A dermatoscopic image of a skin lesion.
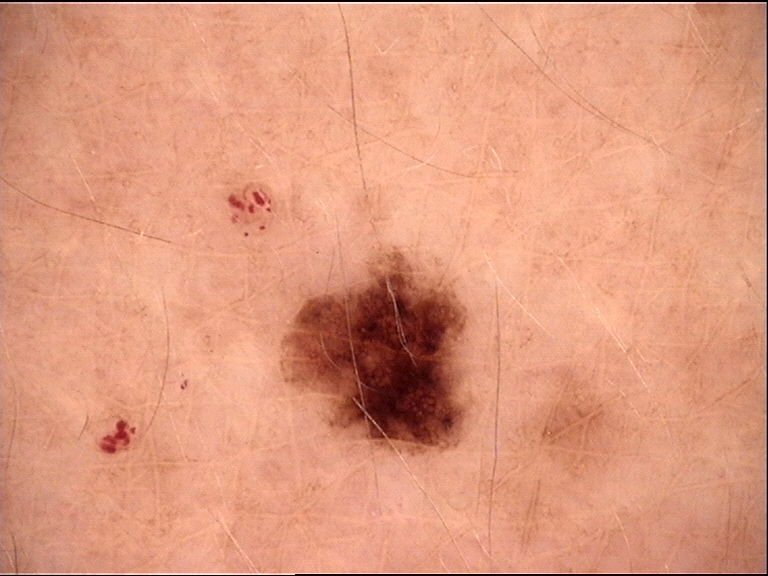Consistent with a benign lesion — a dysplastic junctional nevus.